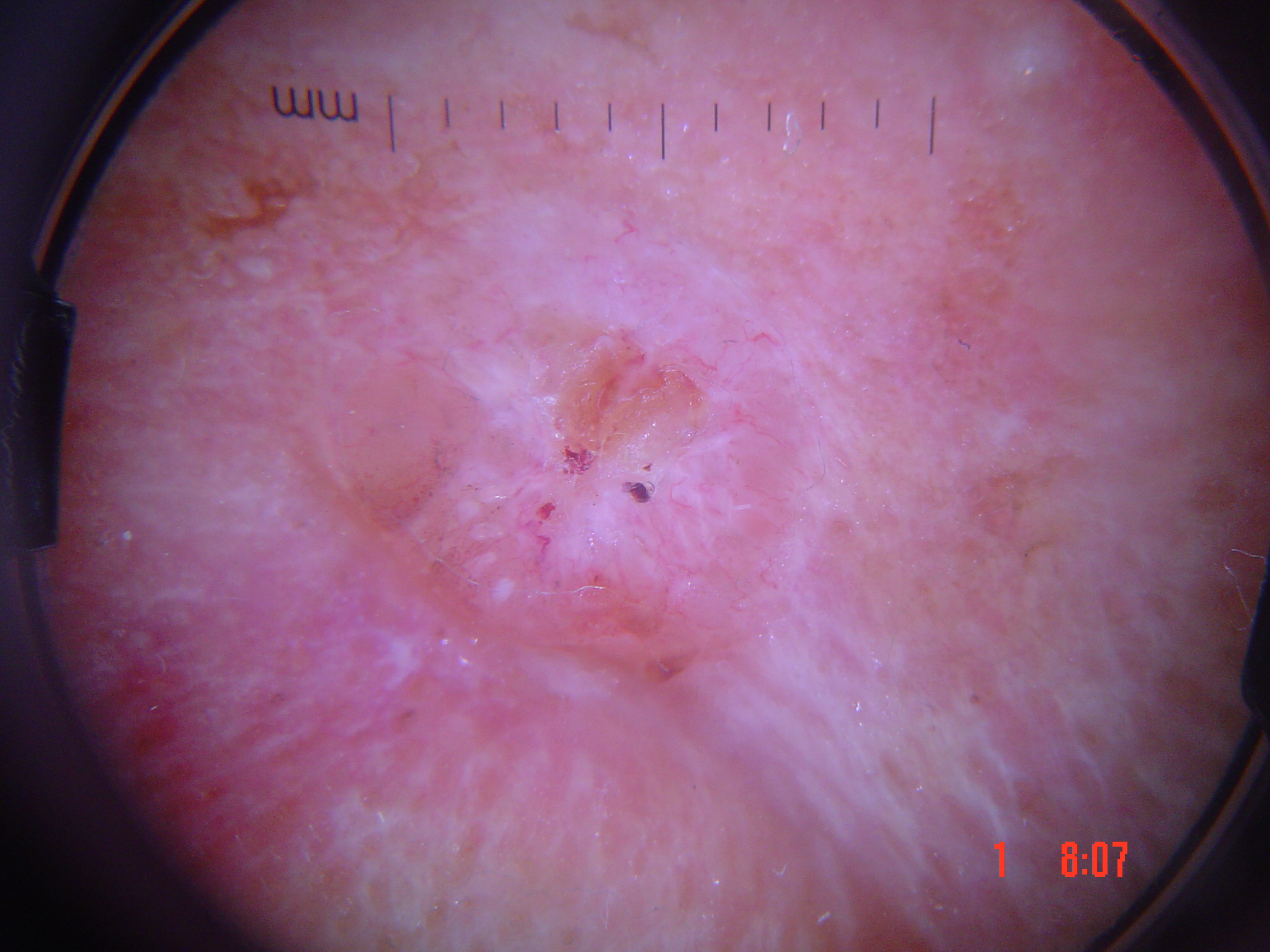A dermoscopy image of a single skin lesion.
The biopsy diagnosis was a malignant, keratinocytic lesion — a basal cell carcinoma.